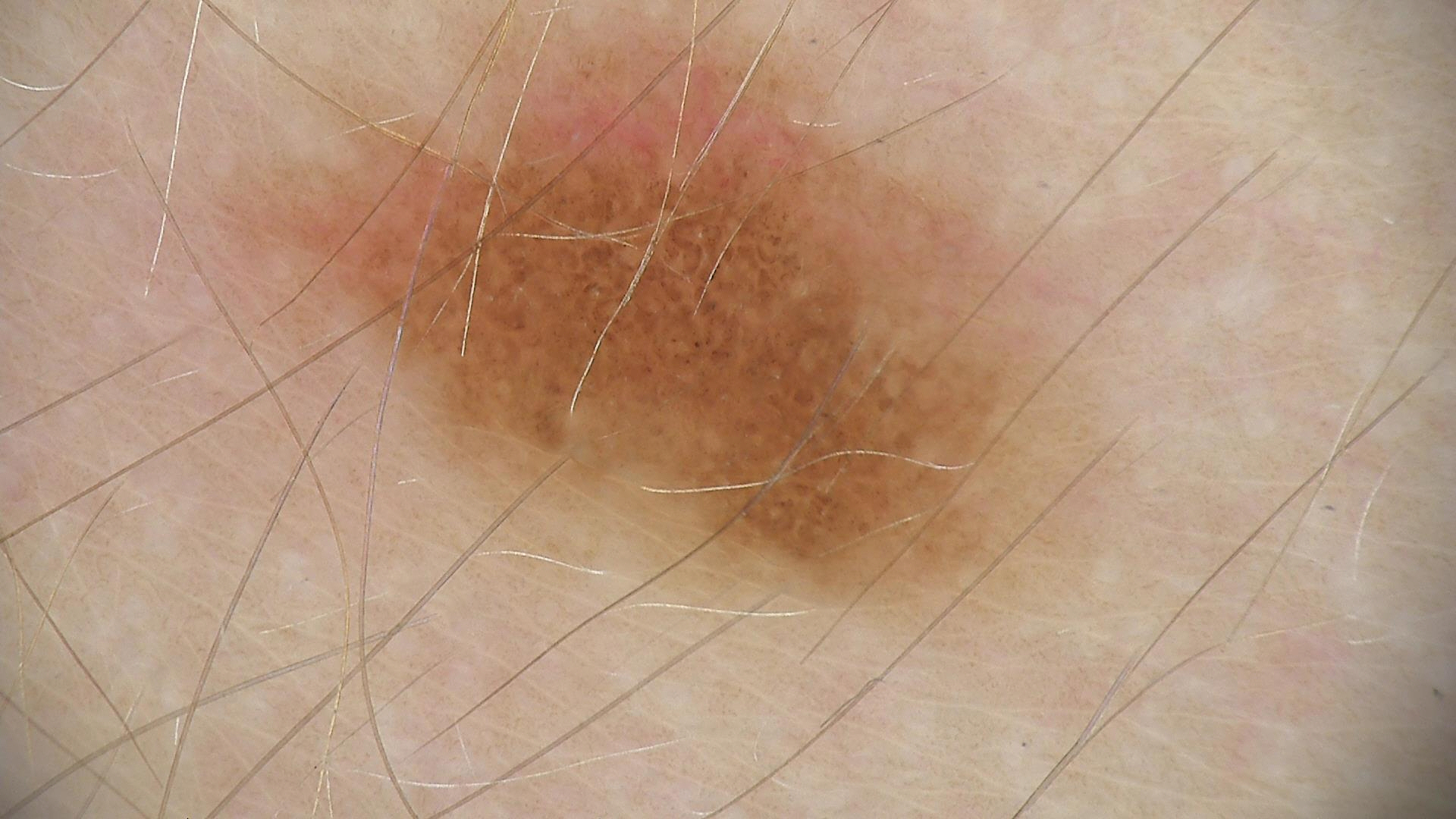image: dermoscopy; label: compound nevus (expert consensus).